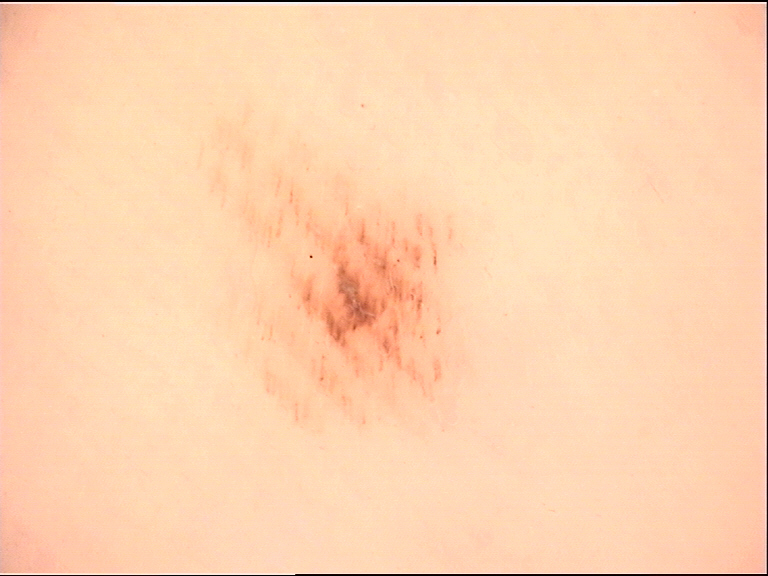modality: dermoscopy | assessment: acral dysplastic junctional nevus (expert consensus).